Texture is reported as raised or bumpy; no relevant systemic symptoms; present for about one day; the affected area is the arm; this image was taken at a distance:
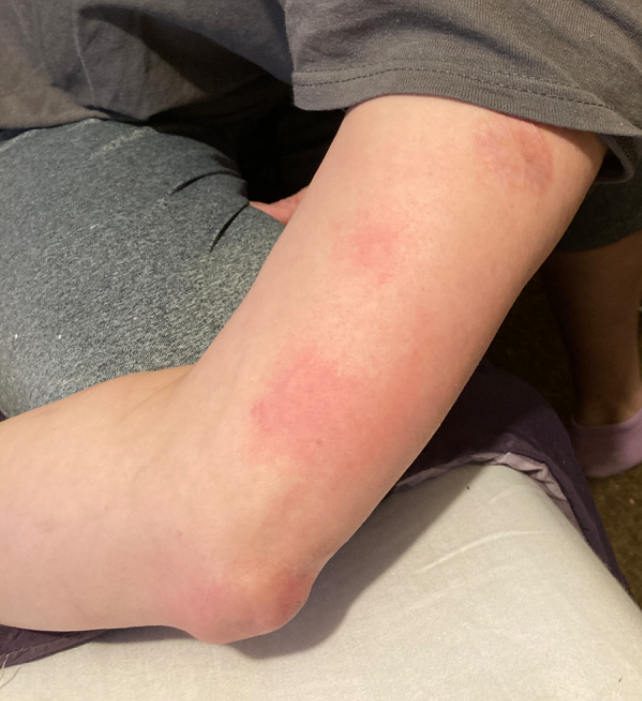Most consistent with Urticaria.